Dermoscopy of a skin lesion: 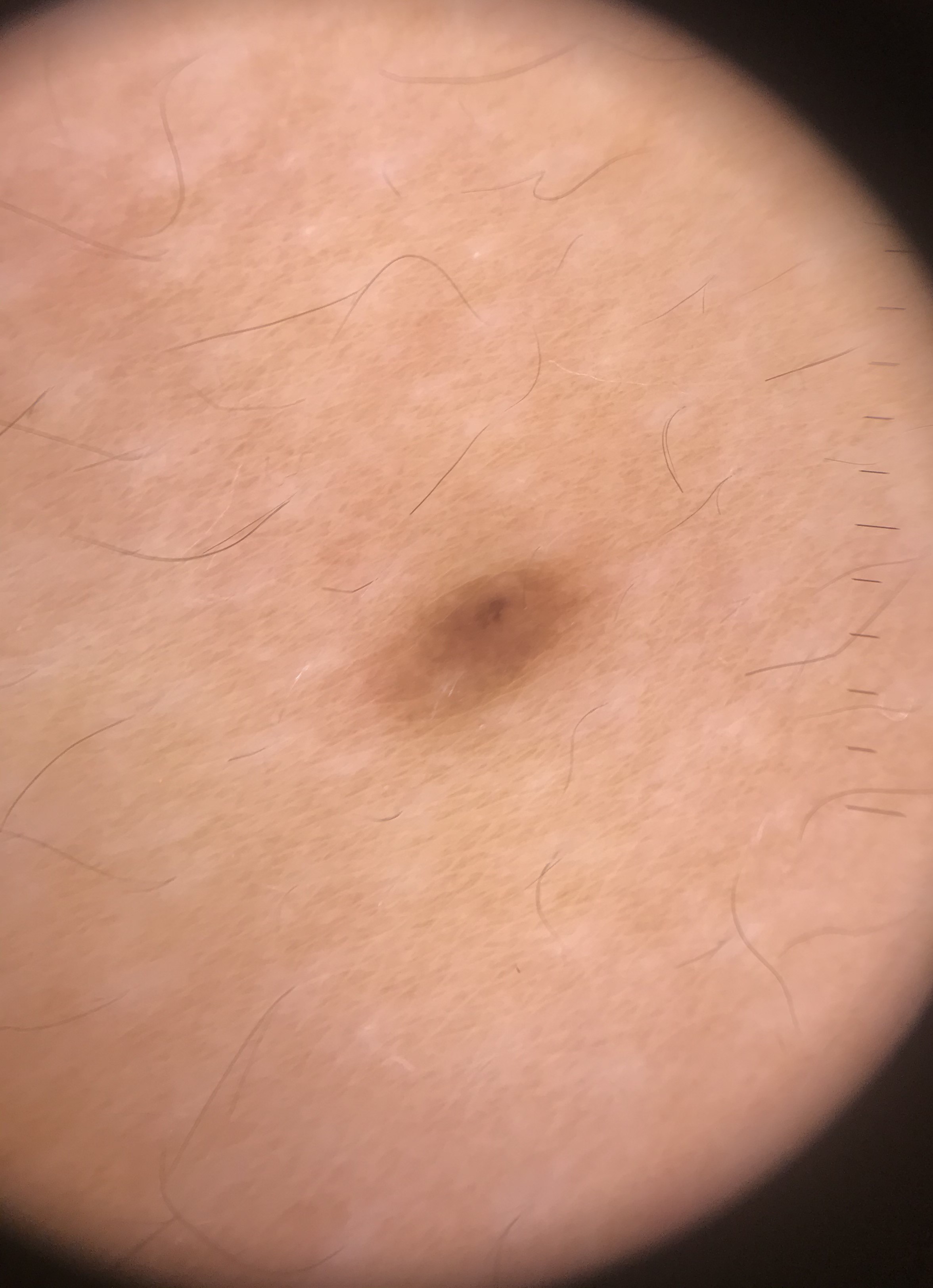The architecture is that of a banal lesion.
Labeled as a junctional nevus.